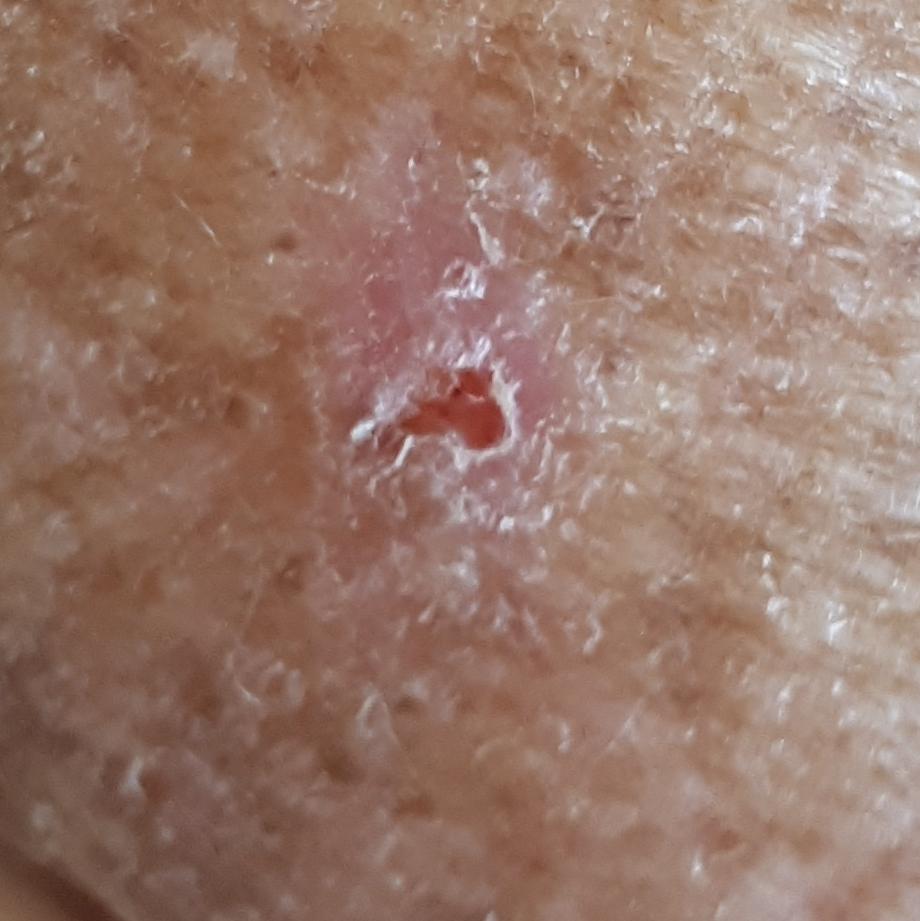{
  "patient": {
    "age": 73
  },
  "image": "smartphone clinical photo",
  "lesion_location": "an arm",
  "symptoms": {
    "present": [
      "itching"
    ]
  },
  "diagnosis": {
    "name": "actinic keratosis",
    "code": "ACK",
    "malignancy": "indeterminate",
    "confirmation": "clinical consensus"
  }
}